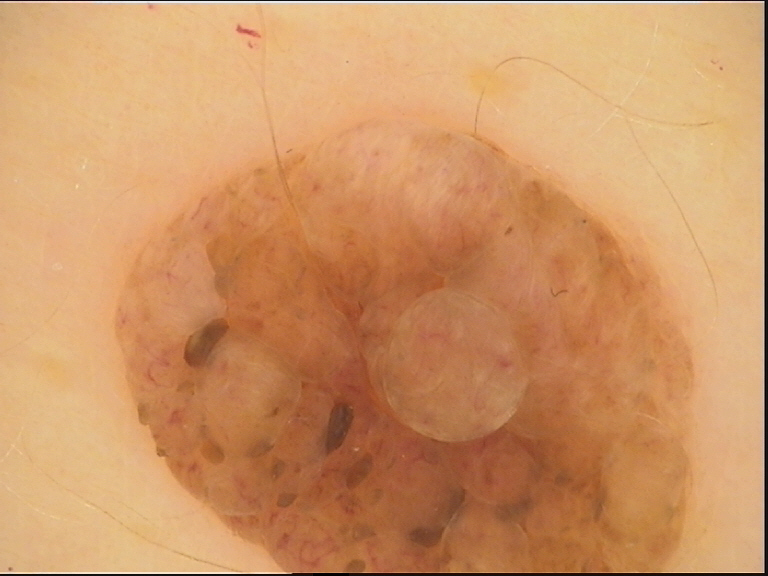Summary: A dermoscopic close-up of a skin lesion. The architecture is that of a banal lesion. Conclusion: Classified as a dermal nevus.